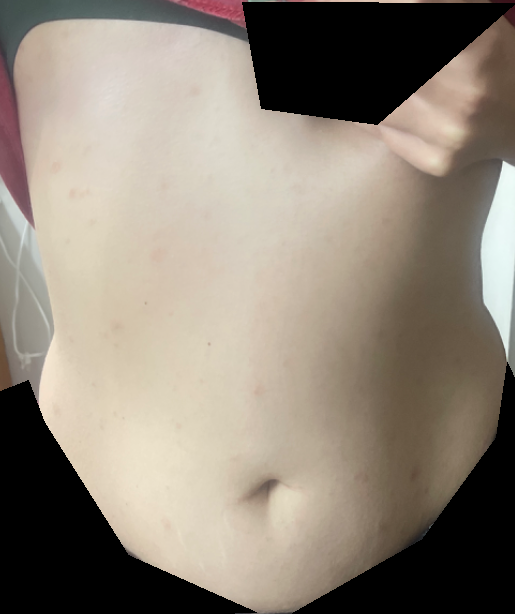differential diagnosis = Pityriasis rosea (55%); Psoriasis (27%); Pityriasis lichenoides (18%)